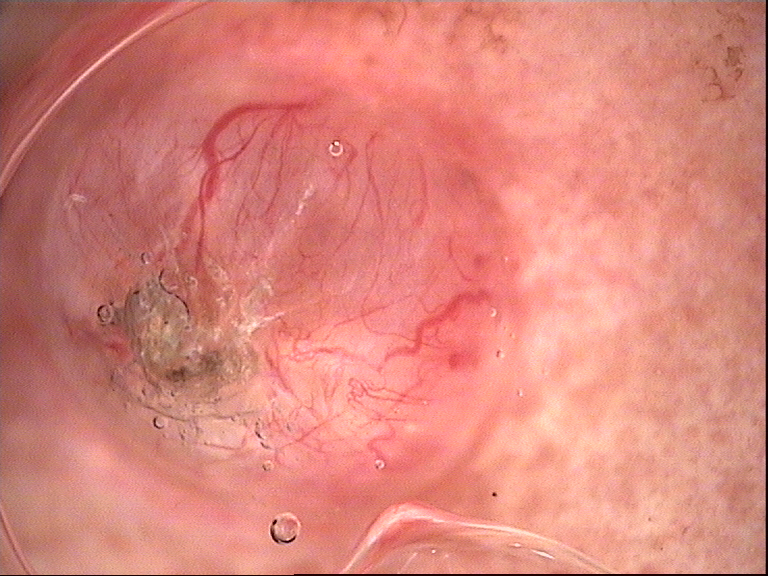Case: A dermatoscopic image of a skin lesion. Conclusion: Confirmed on histopathology as a keratinocytic lesion — a basal cell carcinoma.